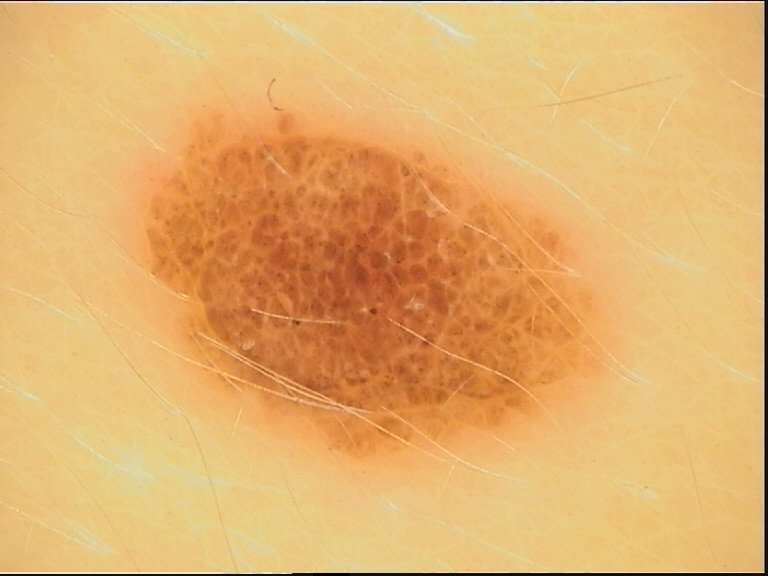Conclusion:
Classified as a compound nevus.